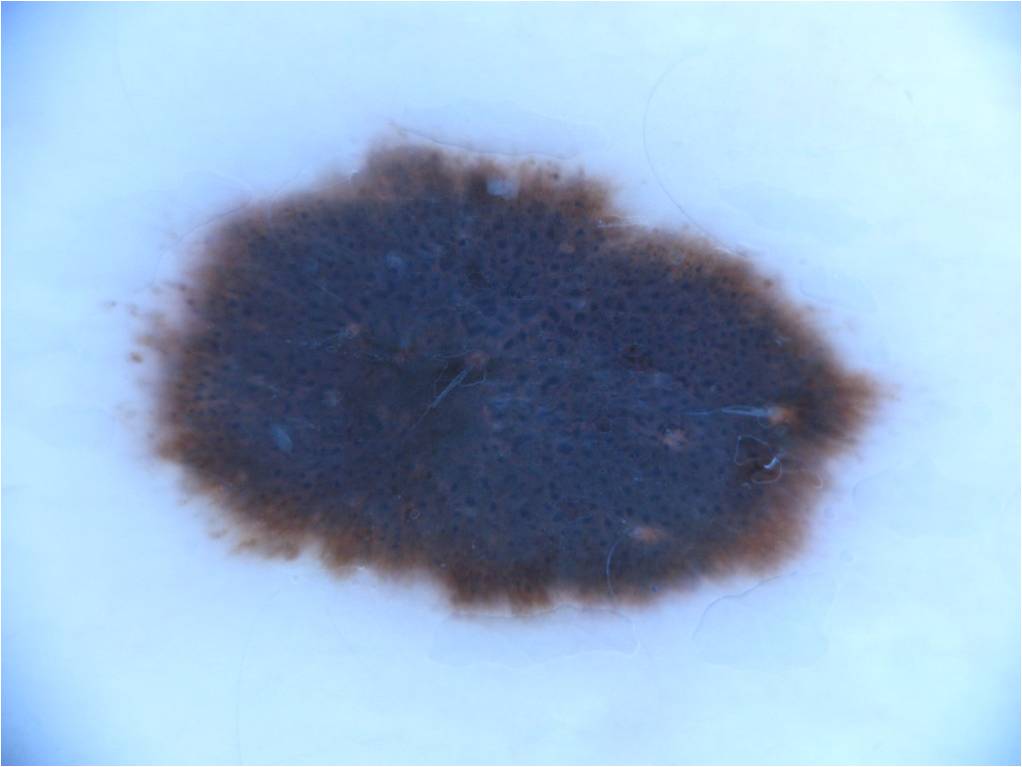The patient is a female in their 20s.
Dermoscopy of a skin lesion.
In (x1, y1, x2, y2) order, the visible lesion spans 130/128/893/624.
On dermoscopy, the lesion shows streaks, globules, and pigment network; no negative network or milia-like cysts.
The diagnostic assessment was a melanocytic nevus.